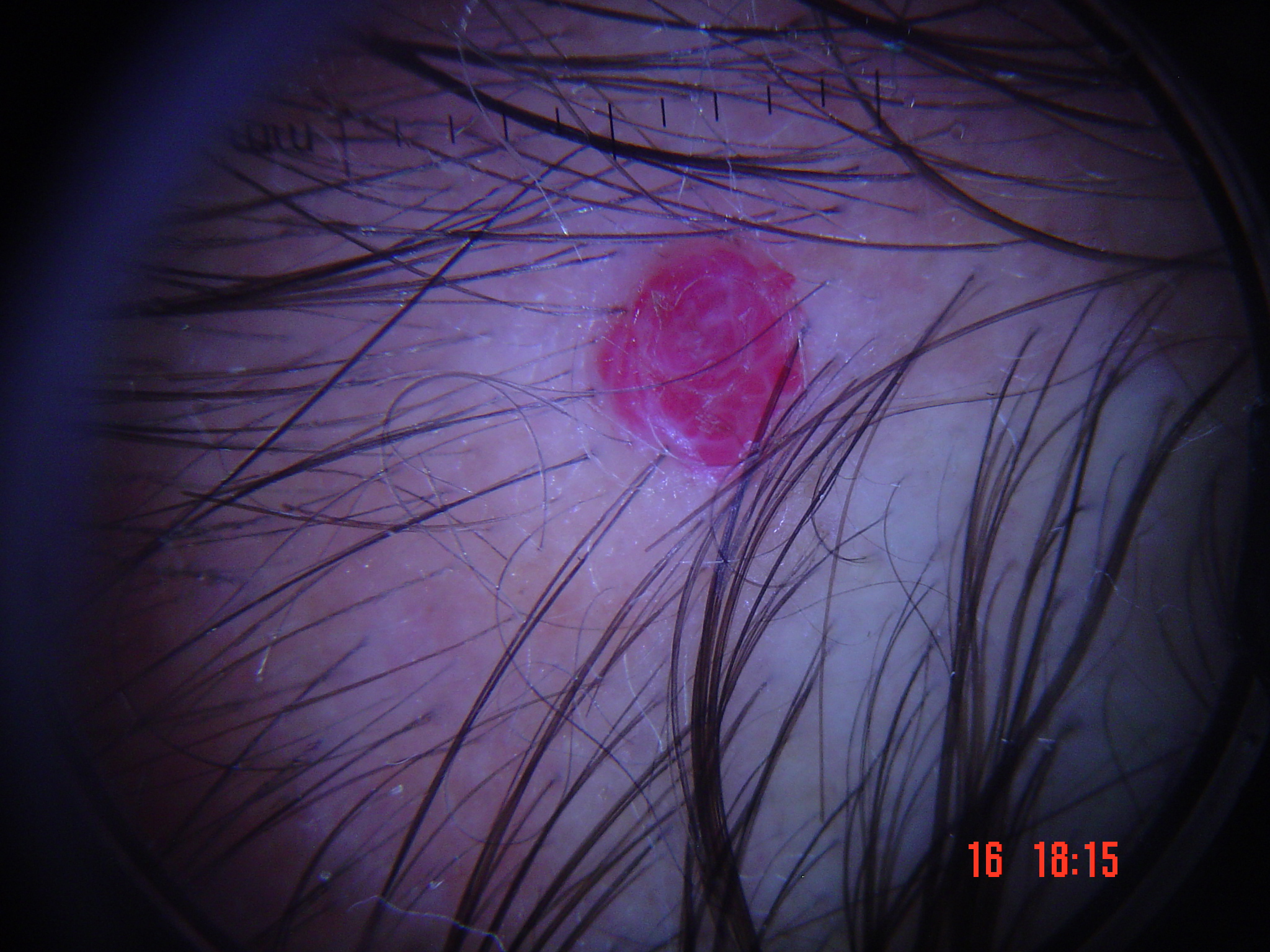Q: What kind of image is this?
A: dermoscopy
Q: What was the diagnostic impression?
A: hemangioma (expert consensus)